An image taken at a distance; the affected area is the leg and top or side of the foot.
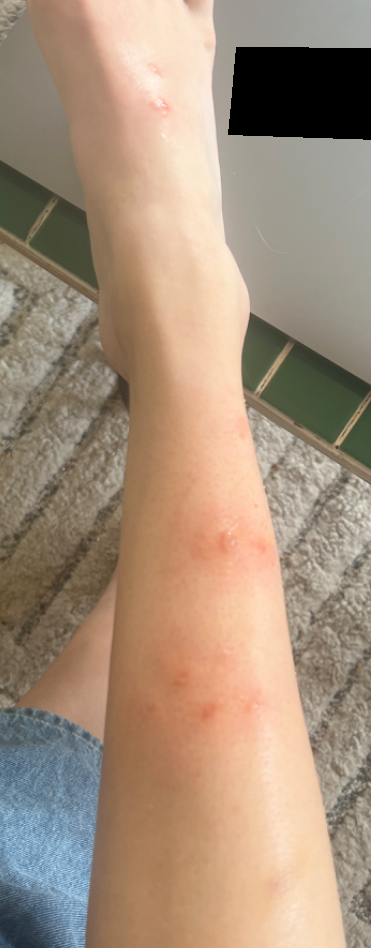{"texture": "fluid-filled", "patient_category": "a rash", "symptoms": ["burning", "itching"], "differential": {"leading": ["Eczema"]}}